A close-up photograph; skin tone: Fitzpatrick skin type I: 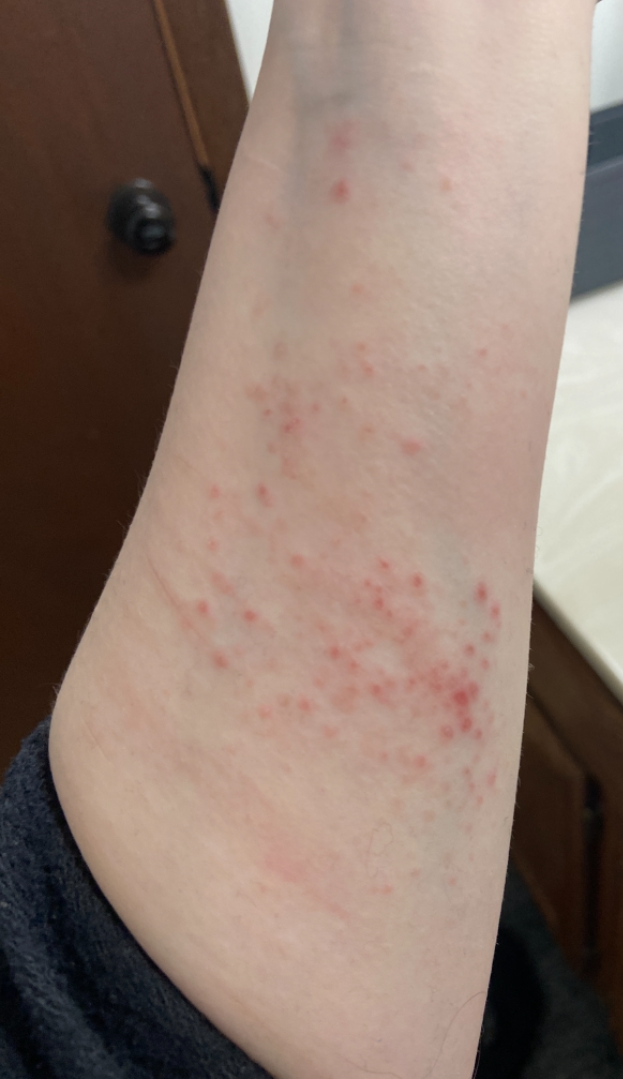<report>
  <differential>
    <leading>Allergic Contact Dermatitis</leading>
  </differential>
</report>